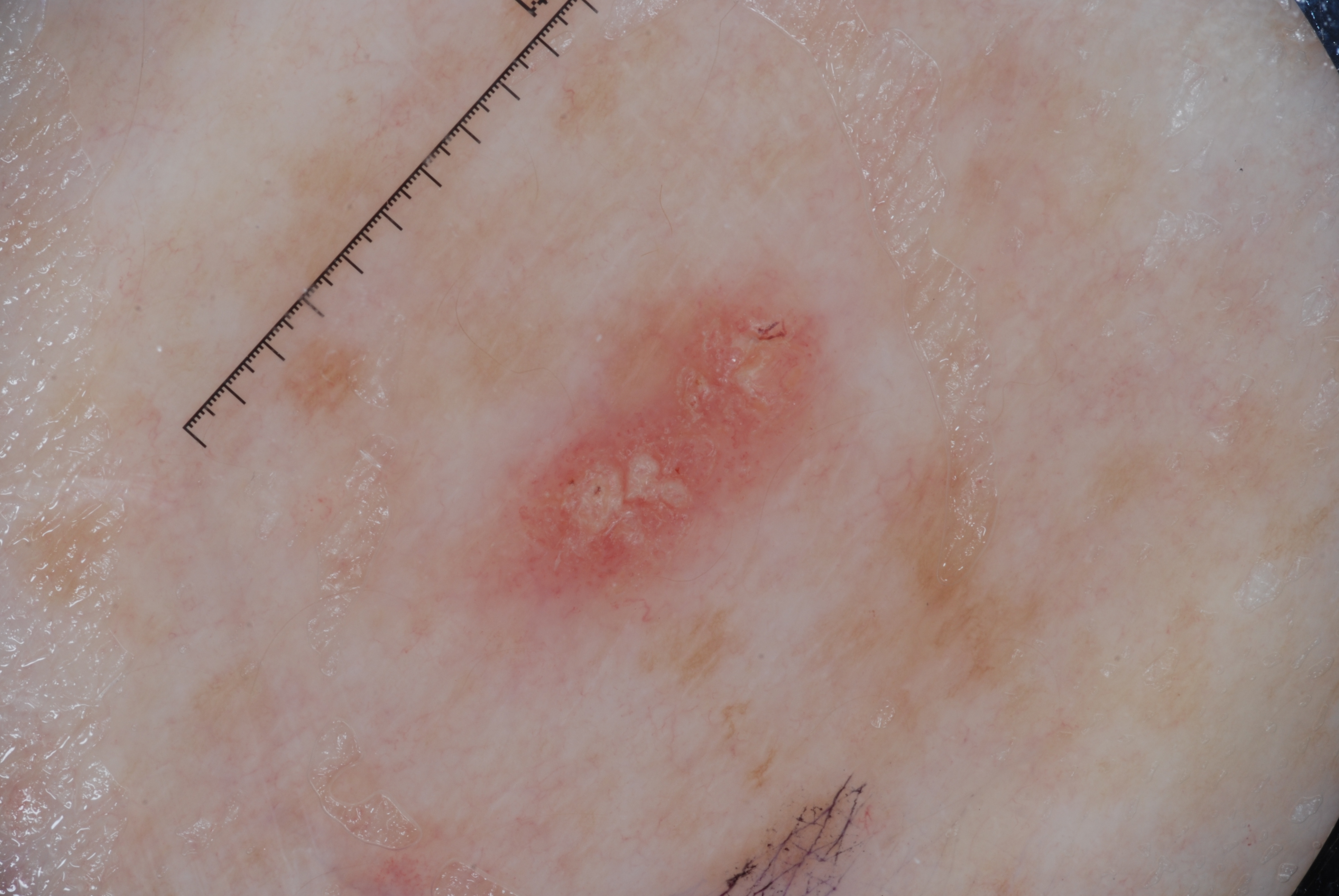A female patient roughly 45 years of age. A dermoscopic view of a skin lesion. The lesion occupies roughly 7% of the field. The lesion's extent is (471, 281, 837, 637). The dermoscopic pattern shows milia-like cysts. Consistent with a seborrheic keratosis, a benign lesion.